Close-up view. The lesion involves the arm, front of the torso, back of the hand and leg.
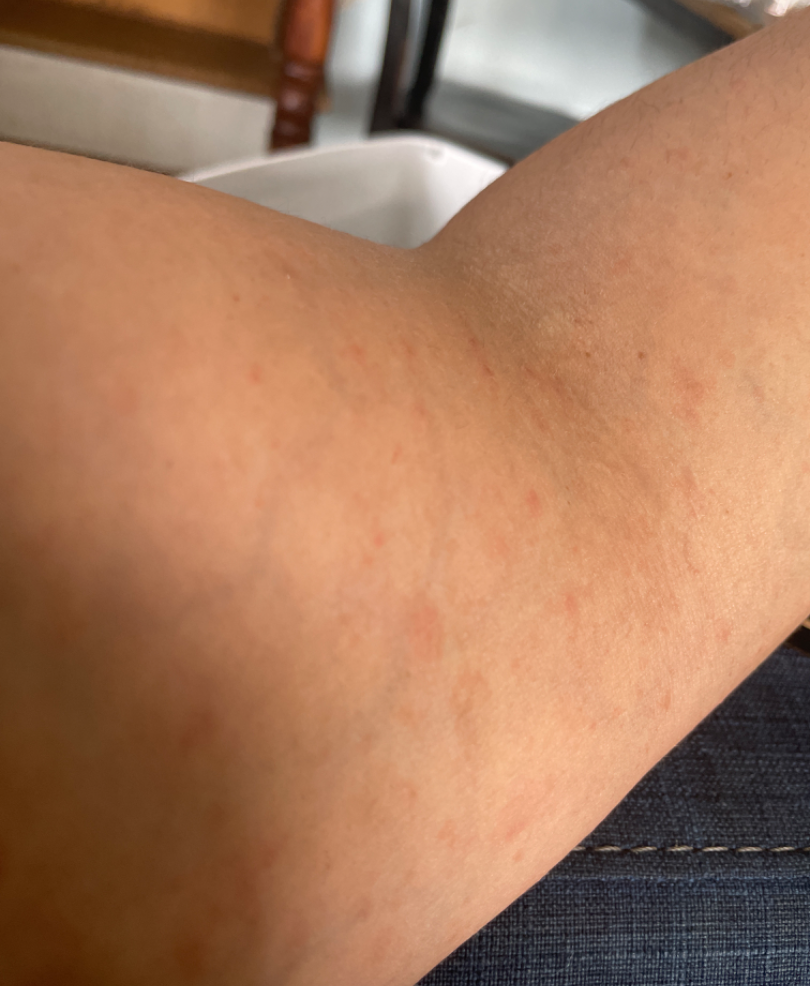The condition could not be reliably identified from the image.
The patient considered this a rash.
Reported lesion symptoms include itching.